A dermoscopy image of a single skin lesion.
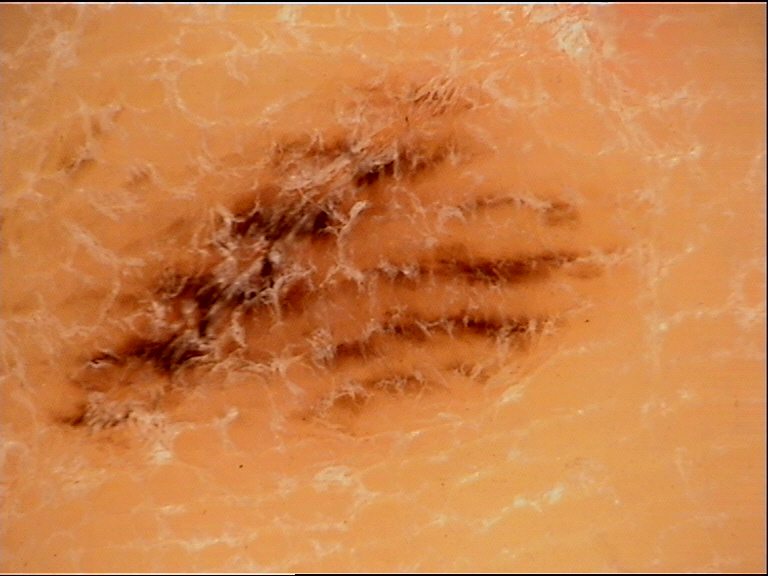Classified as an acral dysplastic junctional nevus.